The photograph is a close-up of the affected area · the lesion involves the back of the torso, front of the torso, back of the hand and arm · the subject is 40–49, male.
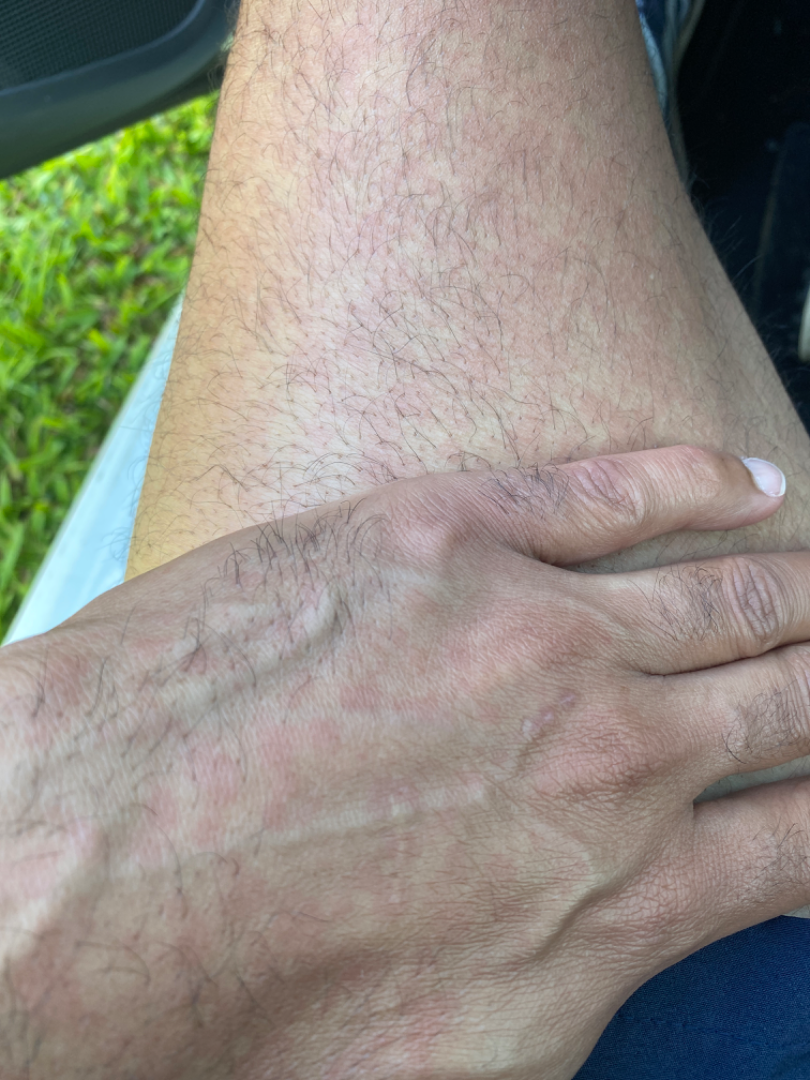| feature | finding |
|---|---|
| texture | flat |
| onset | one to four weeks |
| self-categorized as | skin that appeared healthy to them |
| differential | the favored diagnosis is Drug Rash; possibly Viral Exanthem; less probable is Hypersensitivity; less likely is Photodermatitis; a more distant consideration is Irritant Contact Dermatitis; lower on the differential is Acute dermatitis, NOS |